Texture is reported as rough or flaky; a close-up photograph; self-categorized by the patient as a rash; the contributor is a female aged 60–69; located on the arm: 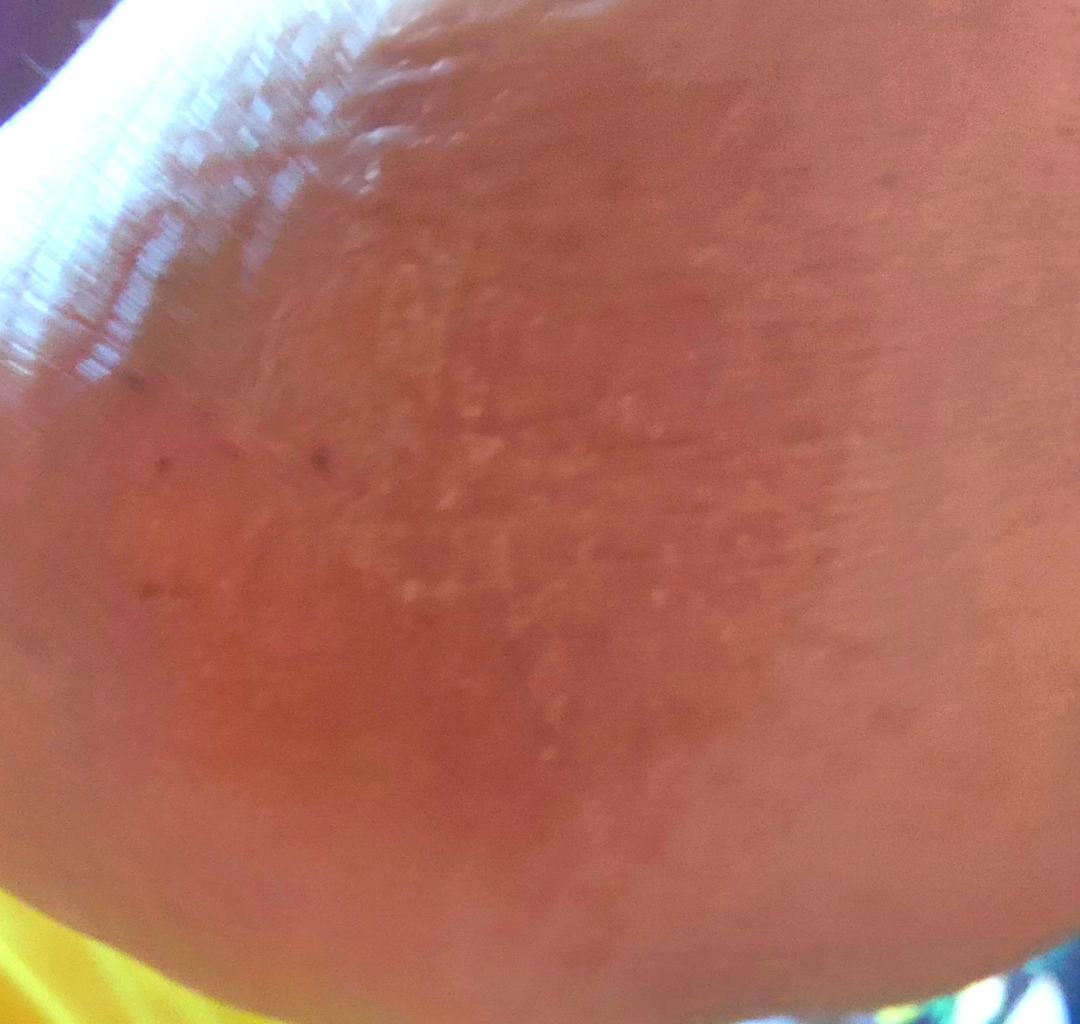<dermatology_case>
<assessment>ungradable on photographic review</assessment>
</dermatology_case>